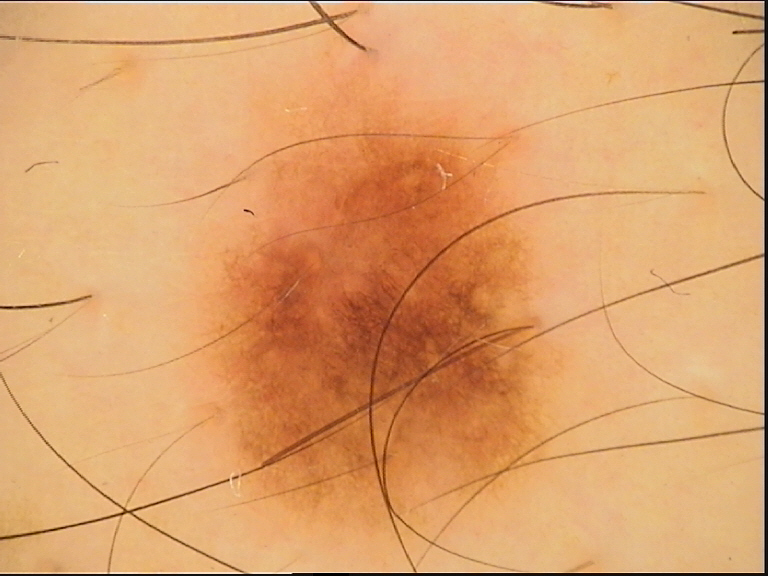Case:
A dermoscopic close-up of a skin lesion.
Conclusion:
Labeled as a benign lesion — a dysplastic junctional nevus.